A dermoscopy image of a single skin lesion · a male subject aged 43 to 47 · recorded as Fitzpatrick phototype II: 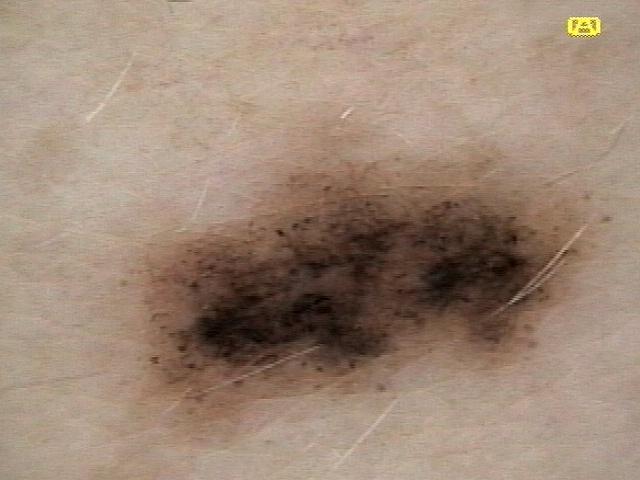The lesion is located on the trunk. The biopsy diagnosis was a nevus.